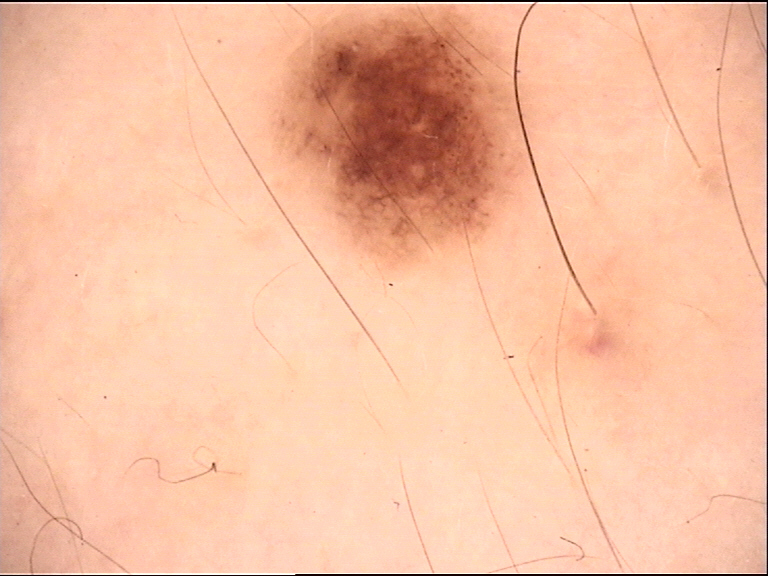class = dysplastic junctional nevus (expert consensus)